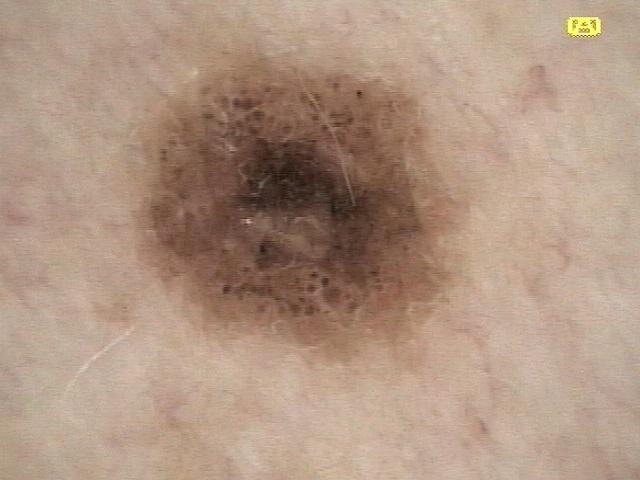A dermoscopic close-up of a skin lesion. The chart notes a previous melanoma. FST II. The lesion is on the trunk, specifically the posterior trunk. Histopathologically confirmed as a melanoma.